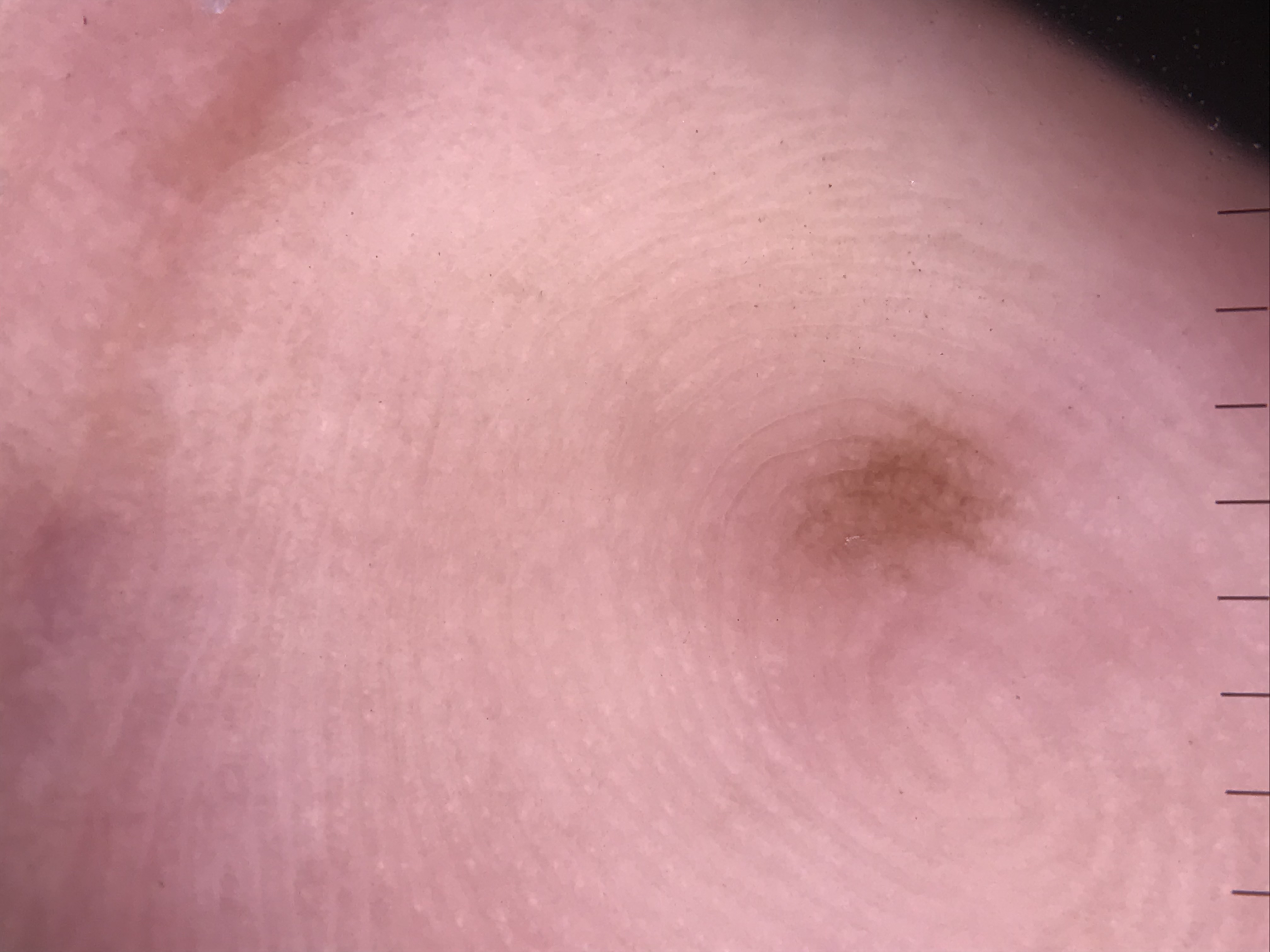Q: What is the imaging modality?
A: dermoscopy
Q: What was the diagnostic impression?
A: acral junctional nevus (expert consensus)